Female patient, age 18–29. Close-up view. The arm is involved. The patient described the issue as a rash. Reported lesion symptoms include burning, enlargement, pain, bothersome appearance and itching. Texture is reported as rough or flaky and raised or bumpy. Skin tone: Fitzpatrick skin type III; human graders estimated MST 1 or 2: 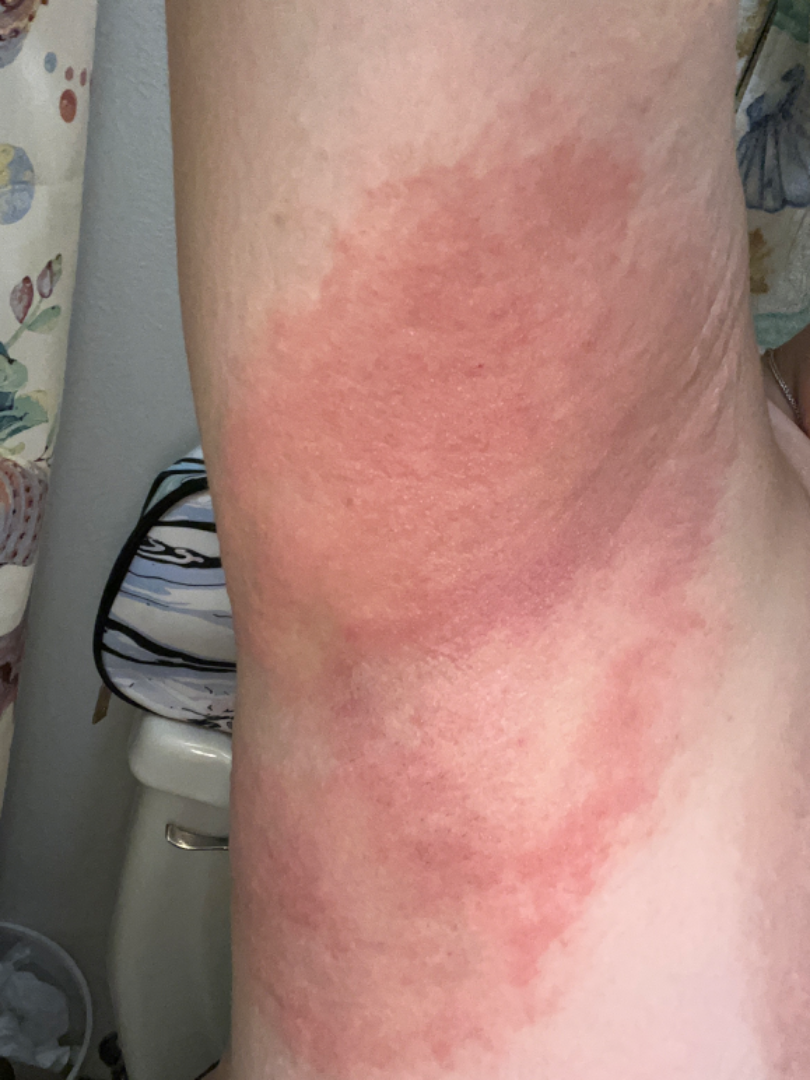Q: What conditions are considered?
A: the leading consideration is Allergic Contact Dermatitis; also on the differential is Irritant Contact Dermatitis